The arm is involved; the condition has been present for about one day; the lesion is described as fluid-filled; this is a close-up image; self-categorized by the patient as skin that appeared healthy to them: 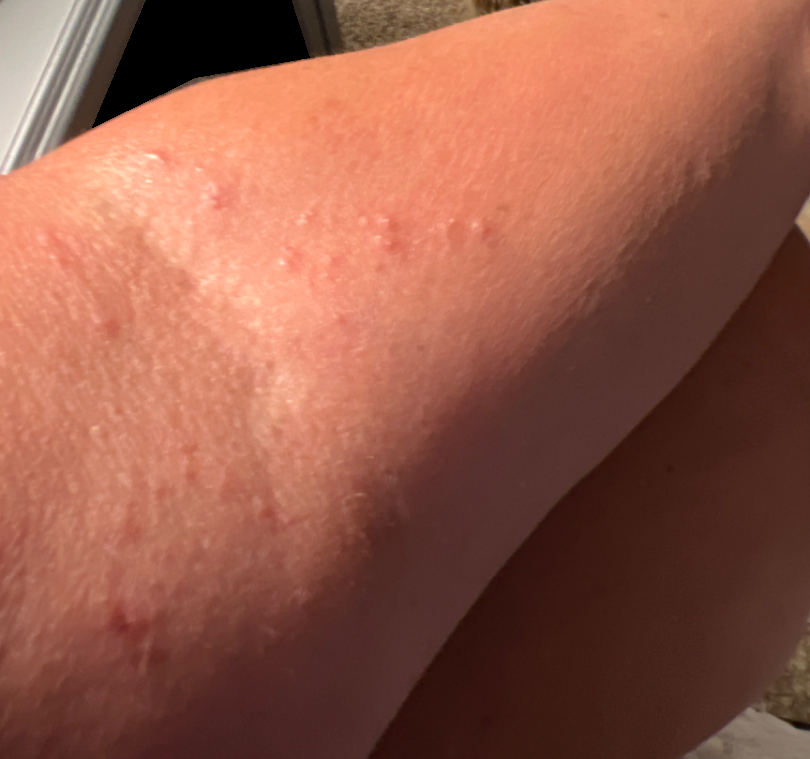On remote dermatologist review: the reviewer's impression was Eczema.